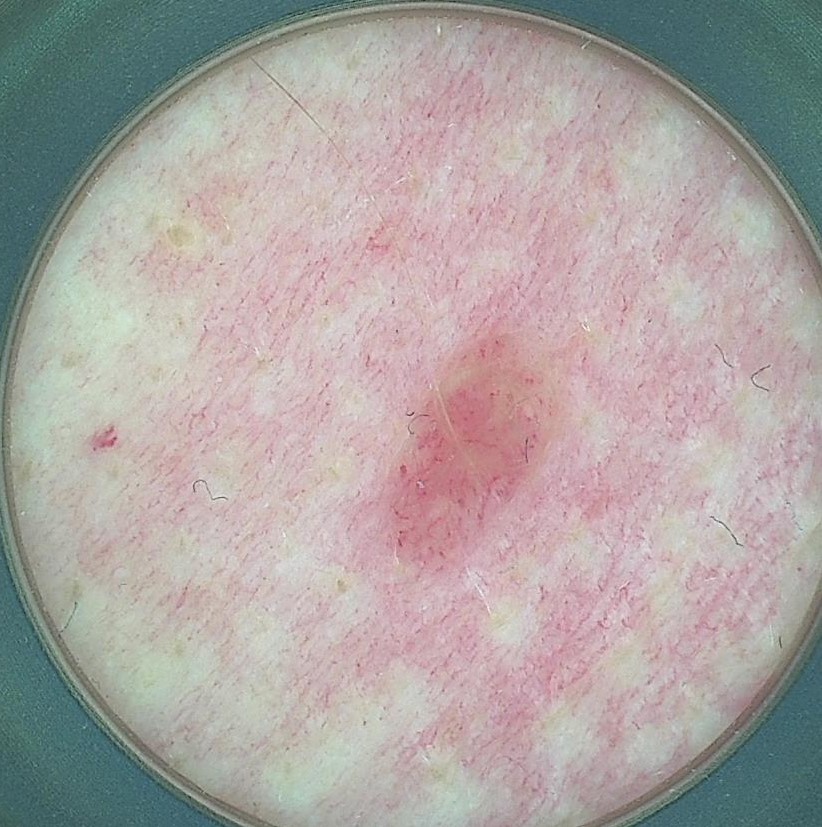| key | value |
|---|---|
| diagnosis | dermal nevus (expert consensus) |